Per the chart, a prior melanoma · contact-polarized dermoscopy of a skin lesion · recorded as skin type II · a male patient in their mid-60s:
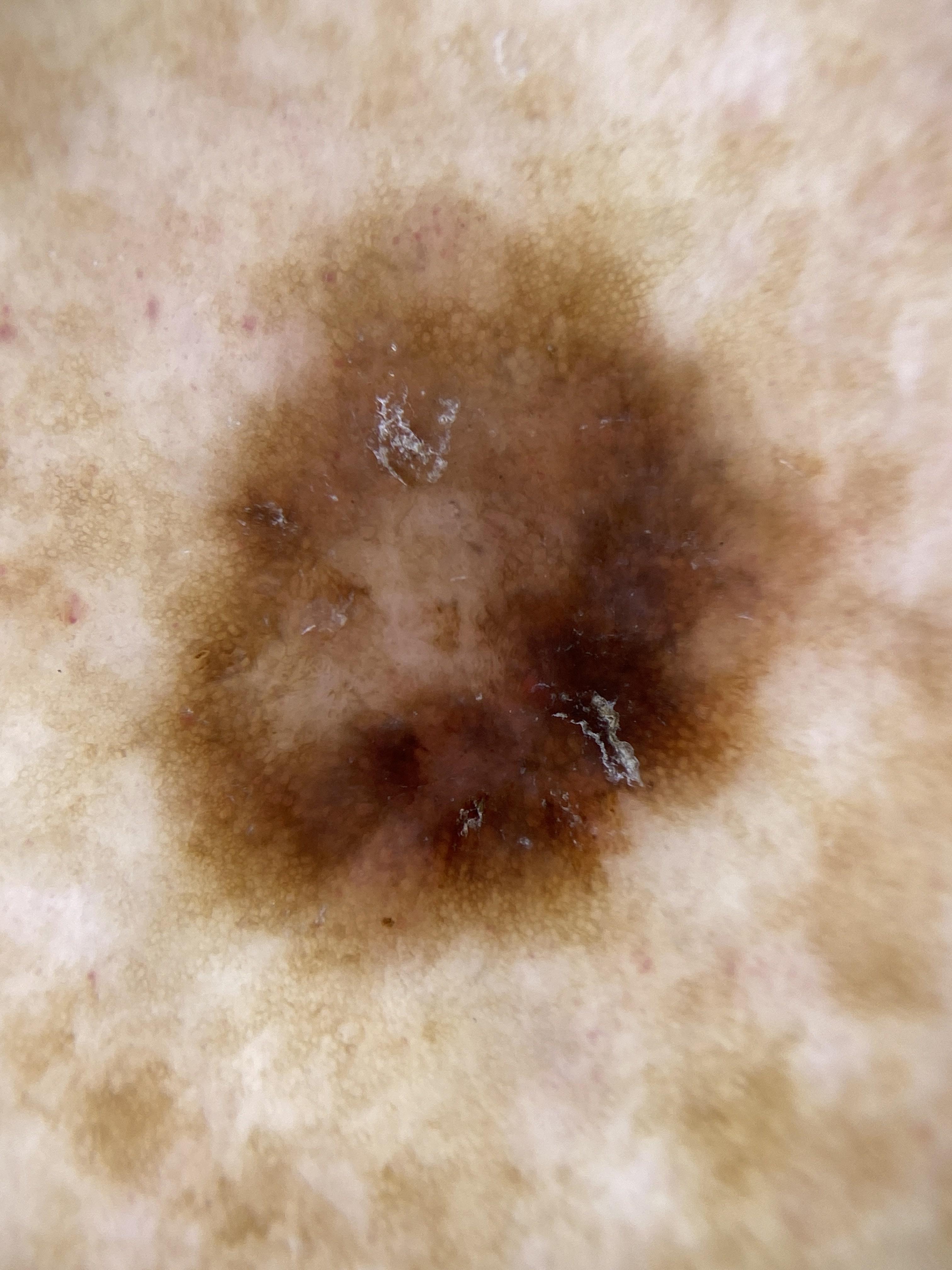site = a lower extremity; diagnostic label = Melanoma (biopsy-proven).